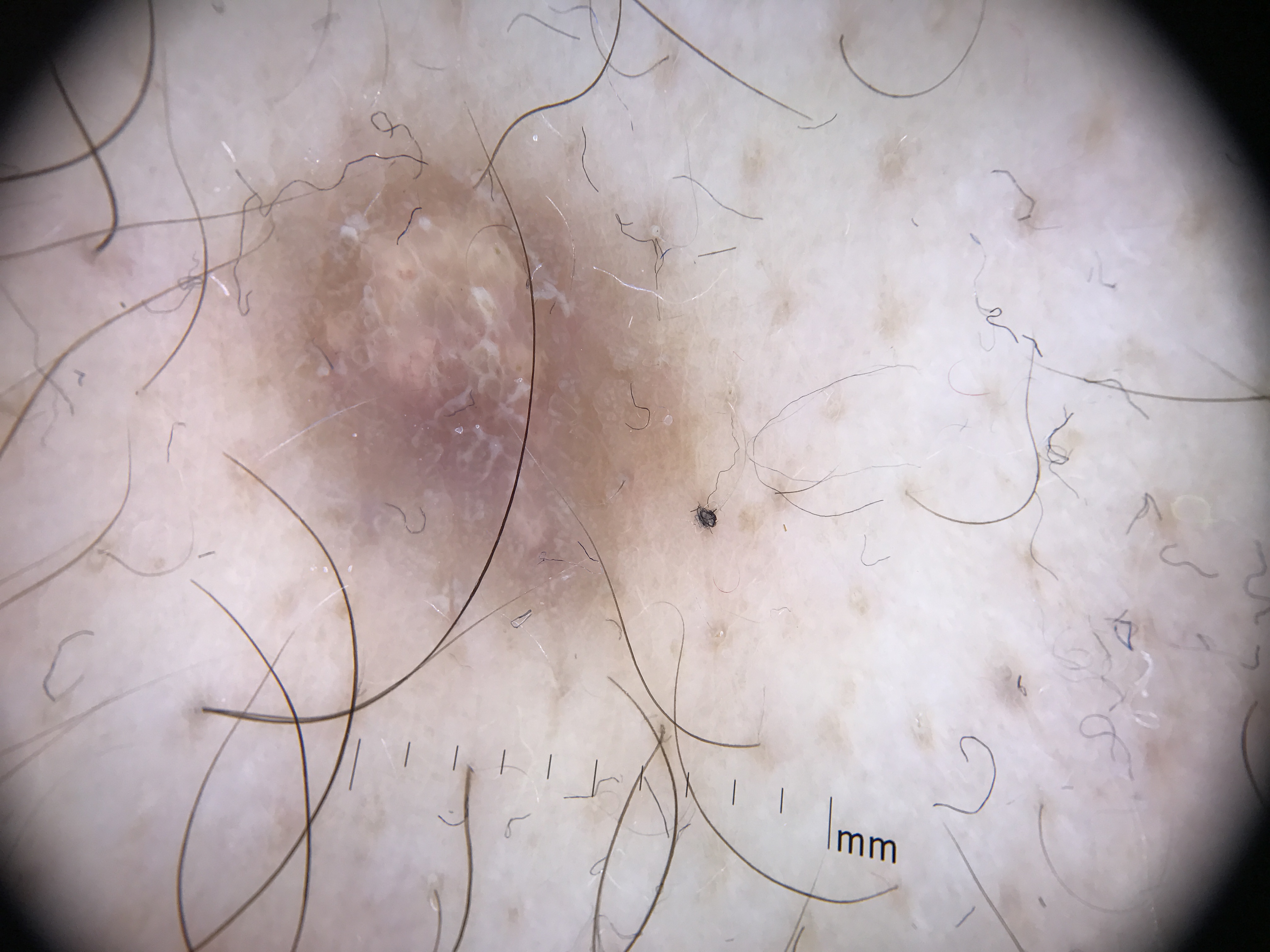Case: A dermoscopic close-up of a skin lesion. This is a fibro-histiocytic lesion. Conclusion: Diagnosed as a dermatofibroma.